Dermoscopy of a skin lesion:
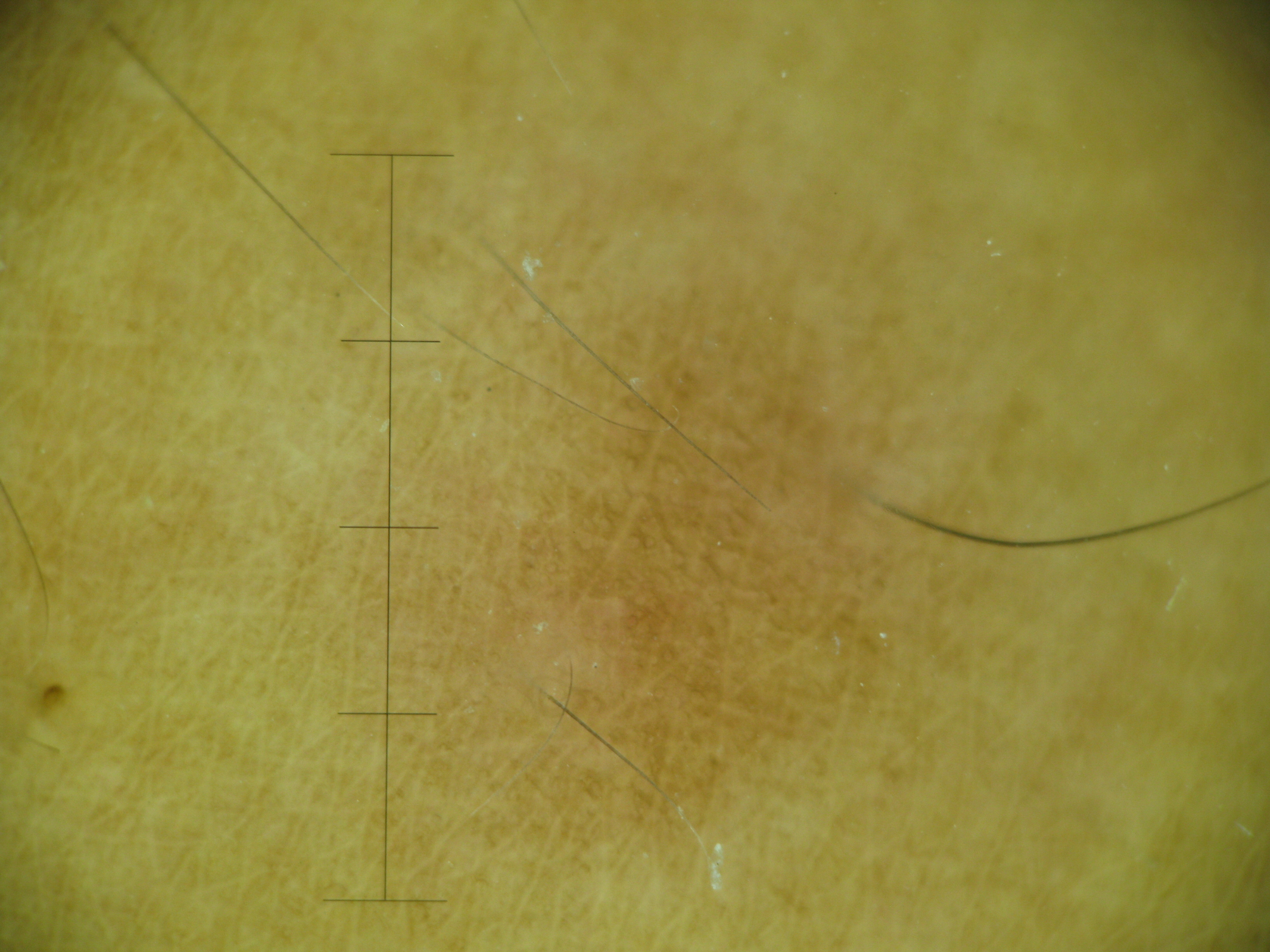Impression:
Classified as a fibro-histiocytic lesion — a dermatofibroma.